Skin type II · a male patient aged approximately 80 · a skin lesion imaged with a dermatoscope:
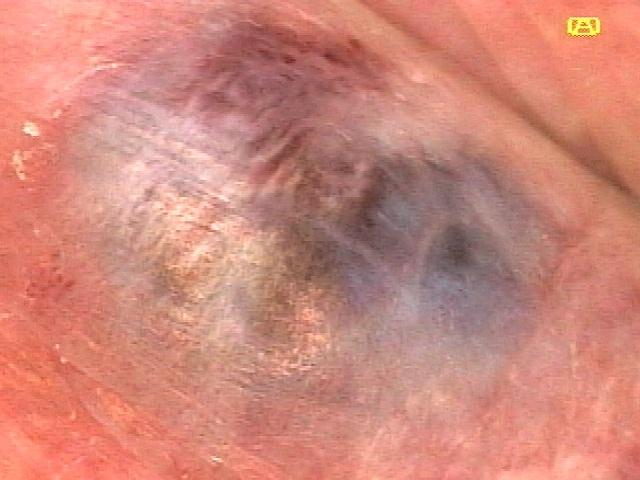<case>
<lesion_location>
<region>the head or neck</region>
</lesion_location>
<diagnosis>
<name>vascular lesion</name>
<malignancy>benign</malignancy>
<confirmation>expert clinical impression</confirmation>
</diagnosis>
</case>